The photo was captured at an angle. Located on the palm and top or side of the foot. The contributor is 18–29, female:
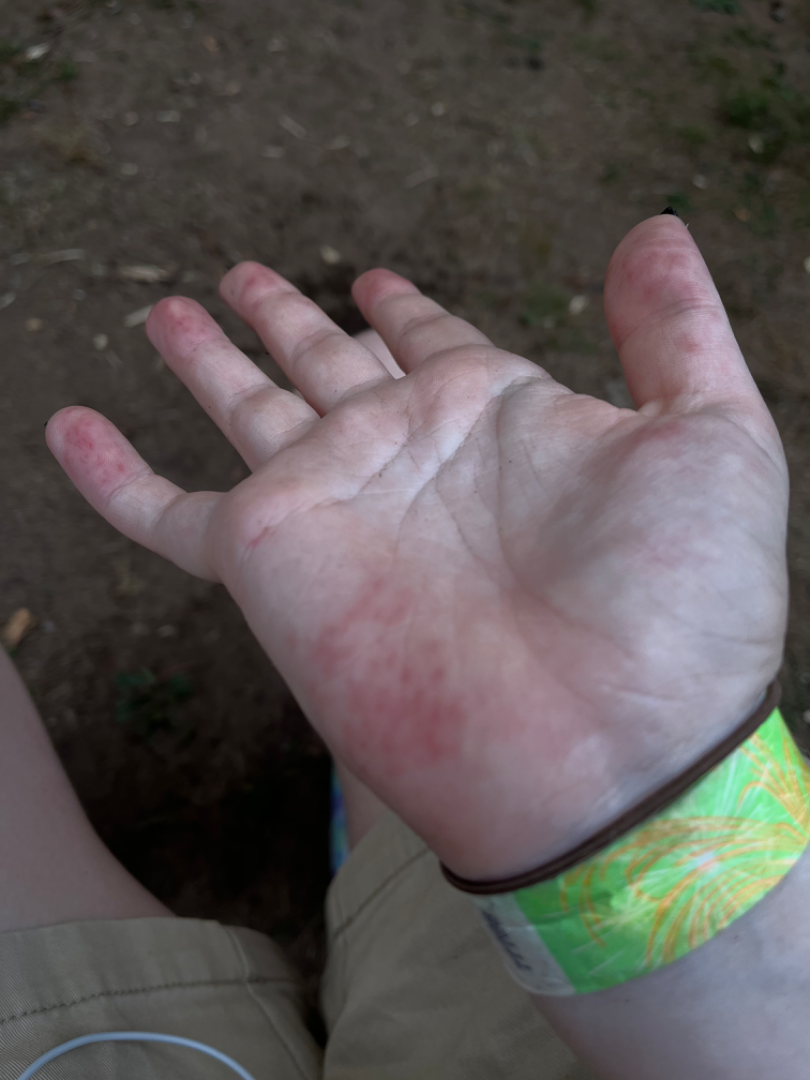assessment: indeterminate
duration: more than one year
patient_category: a rash
texture: flat
symptoms:
  - pain
  - itching